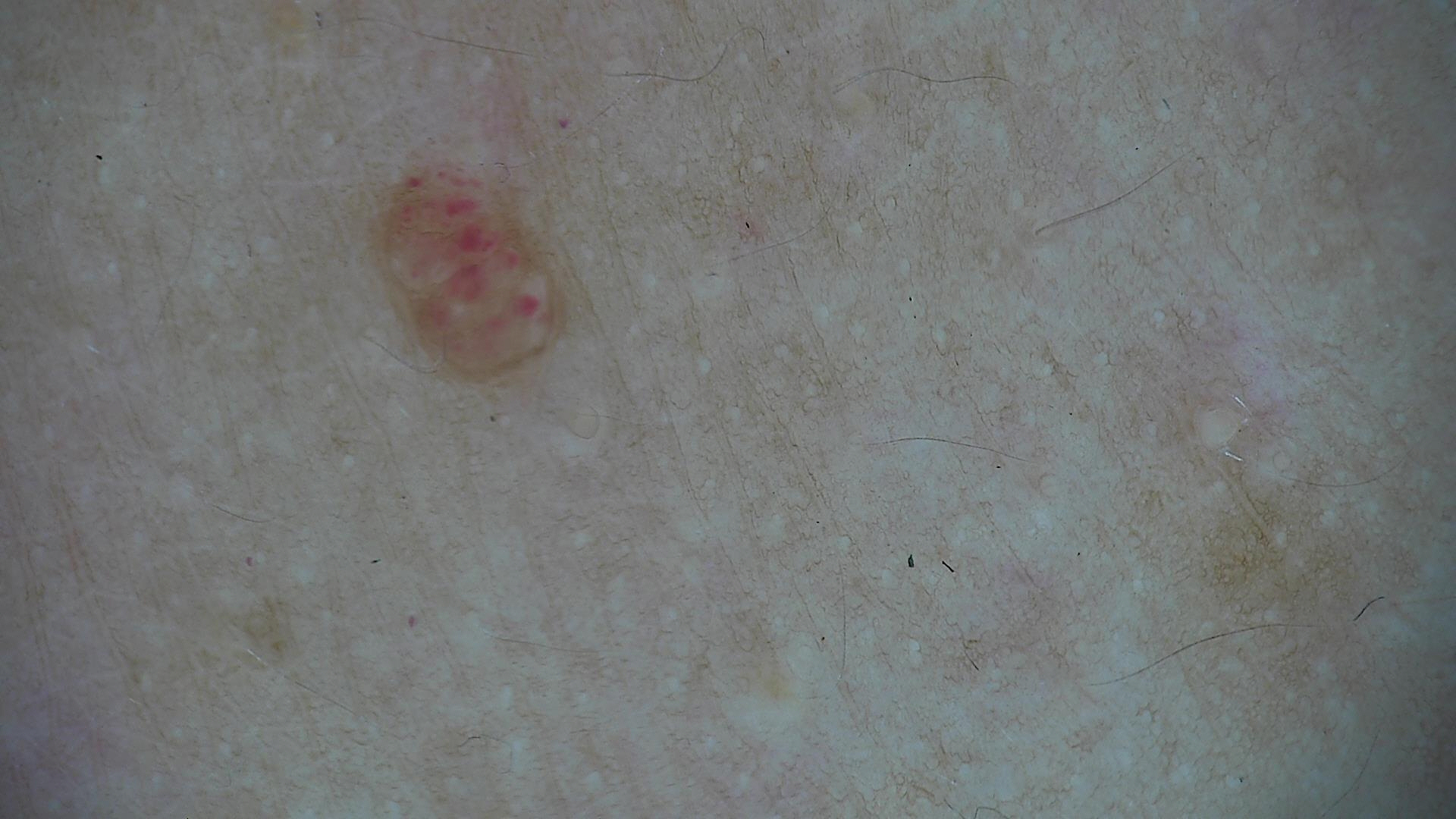The diagnosis was a hemangioma.